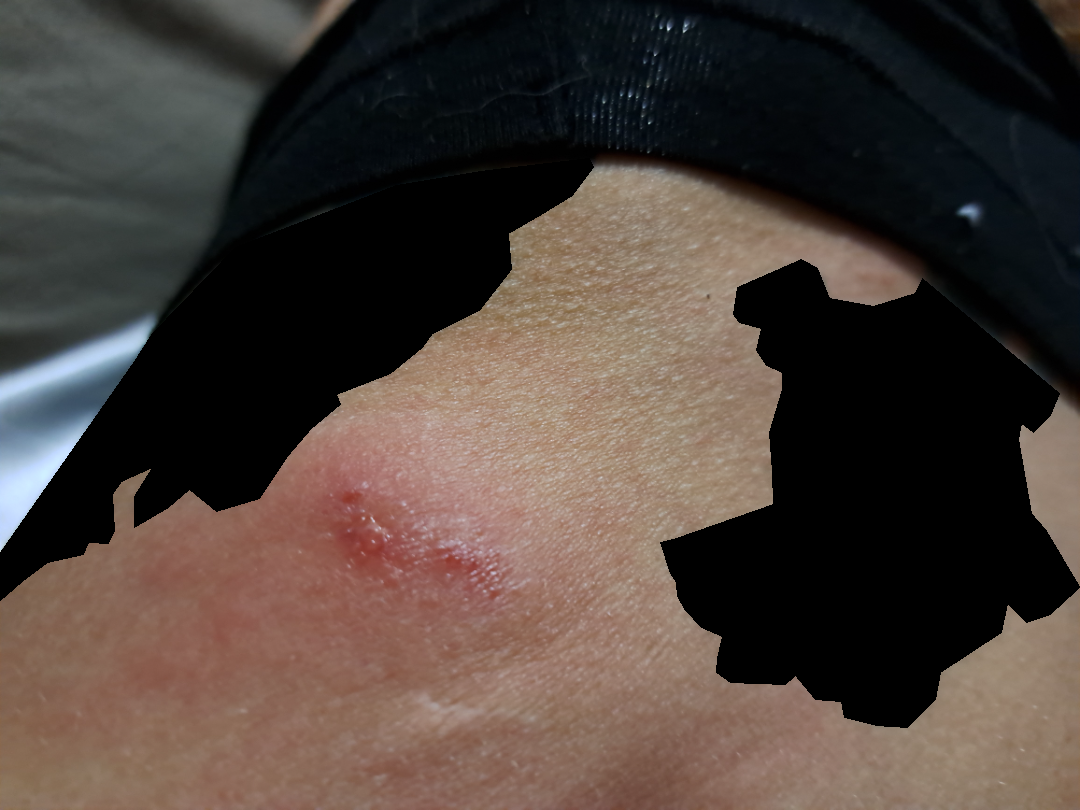assessment: indeterminate
shot type: close-up
anatomic site: back of the torso and front of the torso
contributor: female, age 40–49
history: less than one week
patient's own categorization: a rash
patient-reported symptoms: itching
surface texture: raised or bumpy